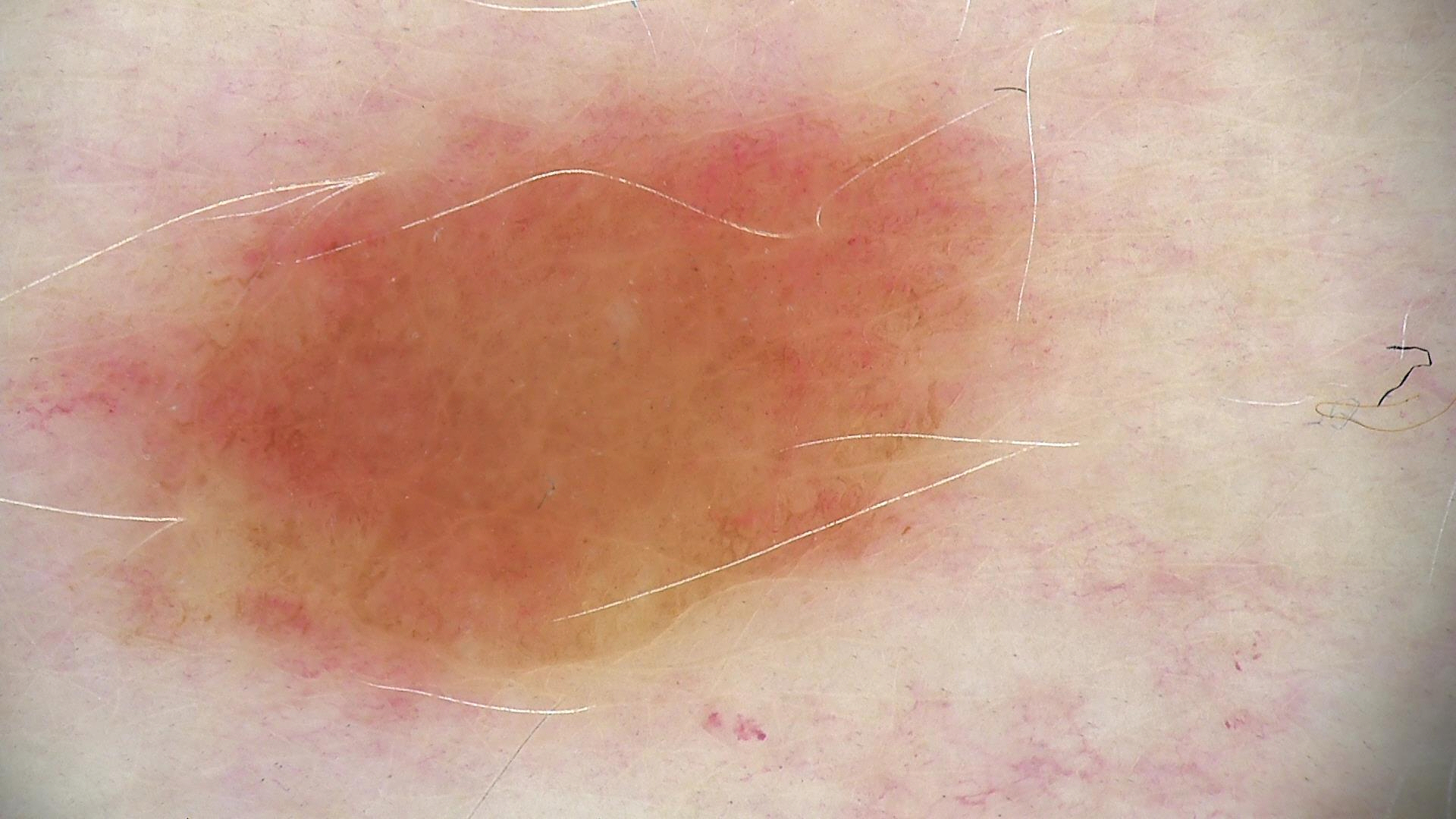image: dermatoscopy | label: dysplastic junctional nevus (expert consensus).